The affected area is the leg · the photograph was taken at a distance:
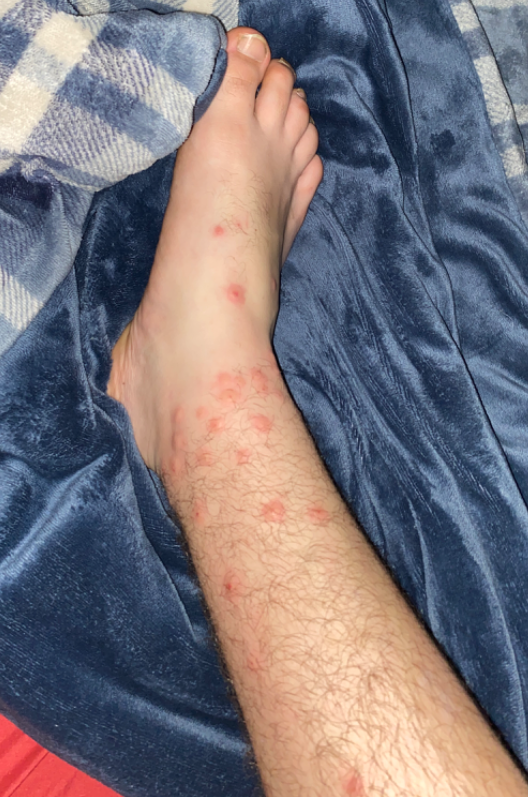Review: The skin findings could not be characterized from the image.